Close-up view · texture is reported as raised or bumpy · the subject is 40–49, female — 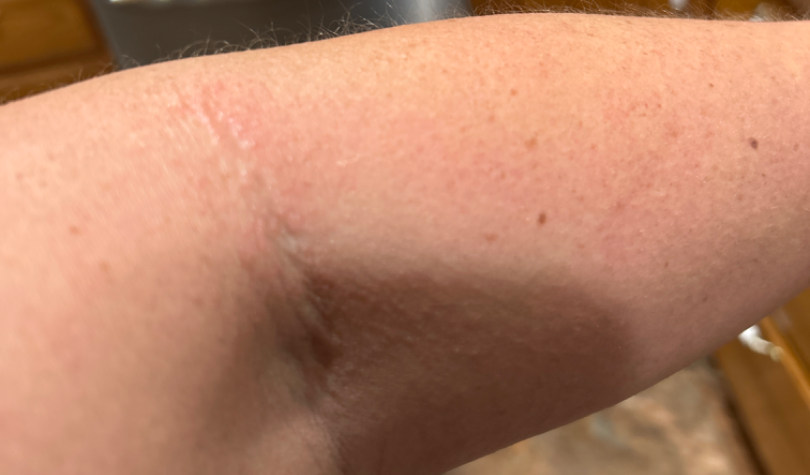Most consistent with Eczema.